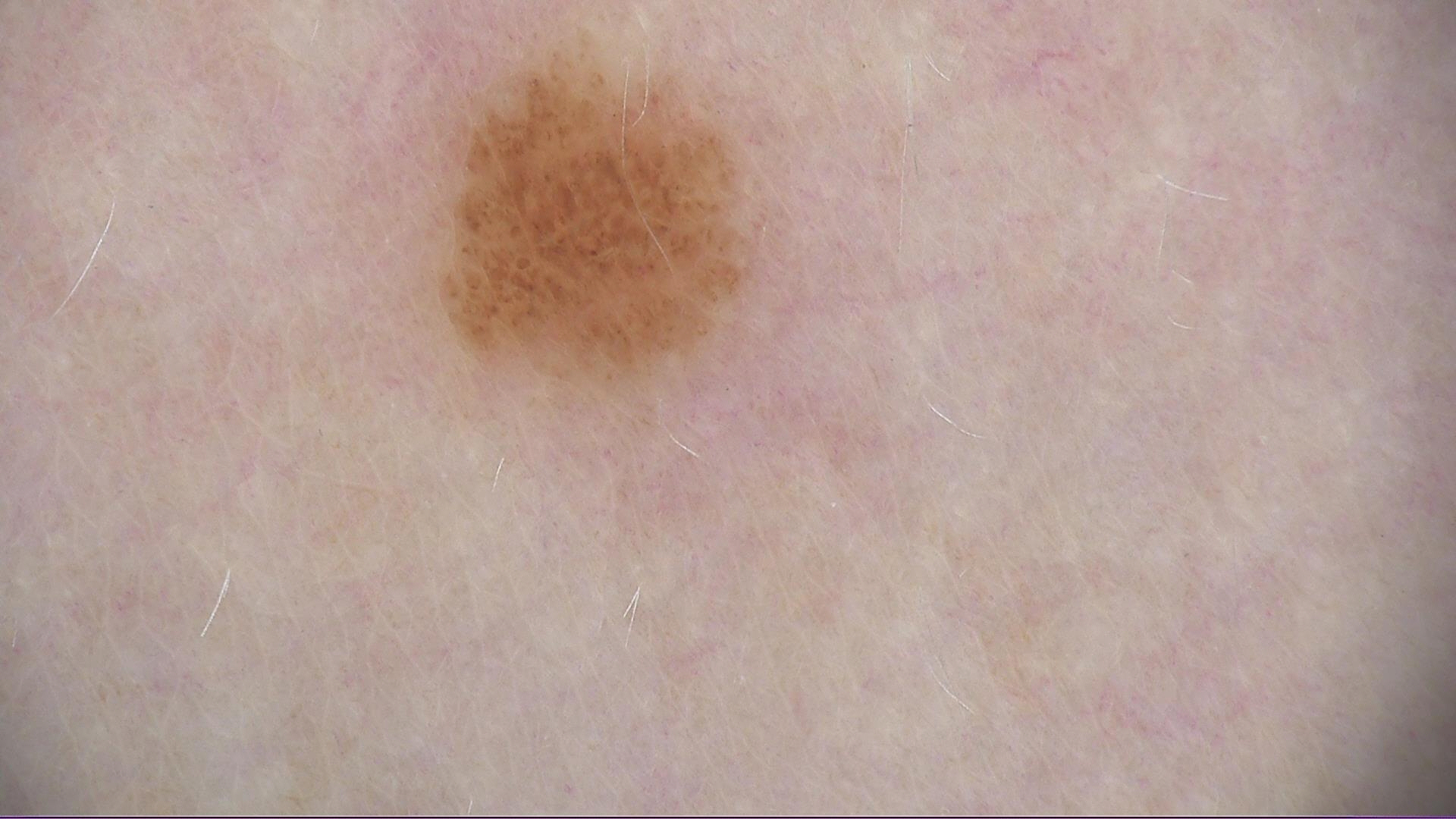Summary: A dermoscopic image of a skin lesion. Conclusion: Labeled as a dysplastic junctional nevus.